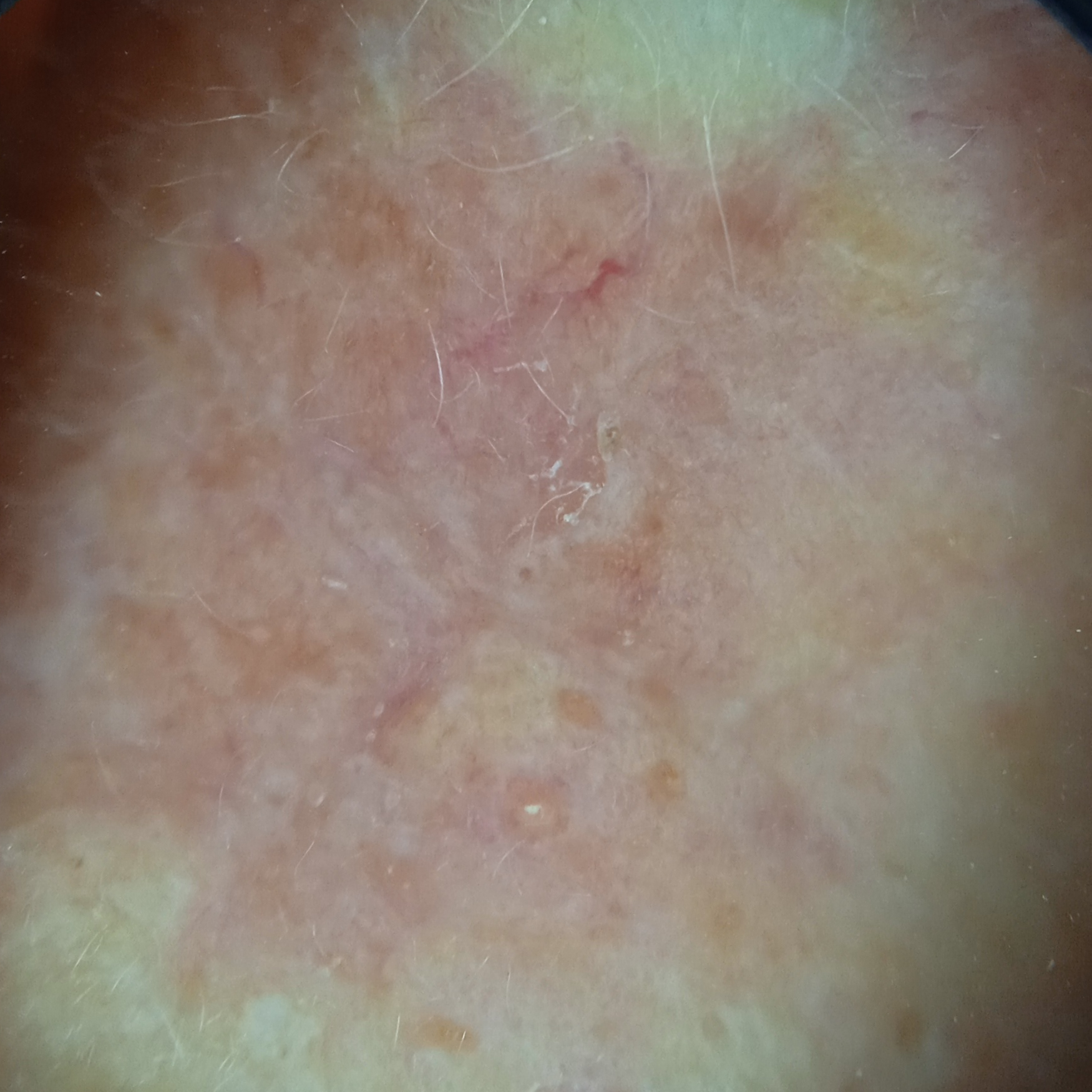| feature | finding |
|---|---|
| nevus count | few melanocytic nevi overall |
| referral context | research study (no referral diagnosis) |
| risk factors | no prior organ transplant, no immunosuppression |
| subject | female, age 68 |
| imaging | dermoscopic image |
| sun reaction | skin tans without first burning |
| location | the face |
| lesion size | 9.9 mm |
| diagnosis | actinic keratosis (dermatologist consensus) |